Reported duration is less than one week. The contributor is 30–39, male. Texture is reported as fluid-filled. Self-categorized by the patient as a rash. Fitzpatrick phototype II; lay reviewers estimated 2 on the Monk skin tone scale. This image was taken at a distance. The patient indicates itching, bothersome appearance, pain and burning. Located on the back of the torso, arm and front of the torso: 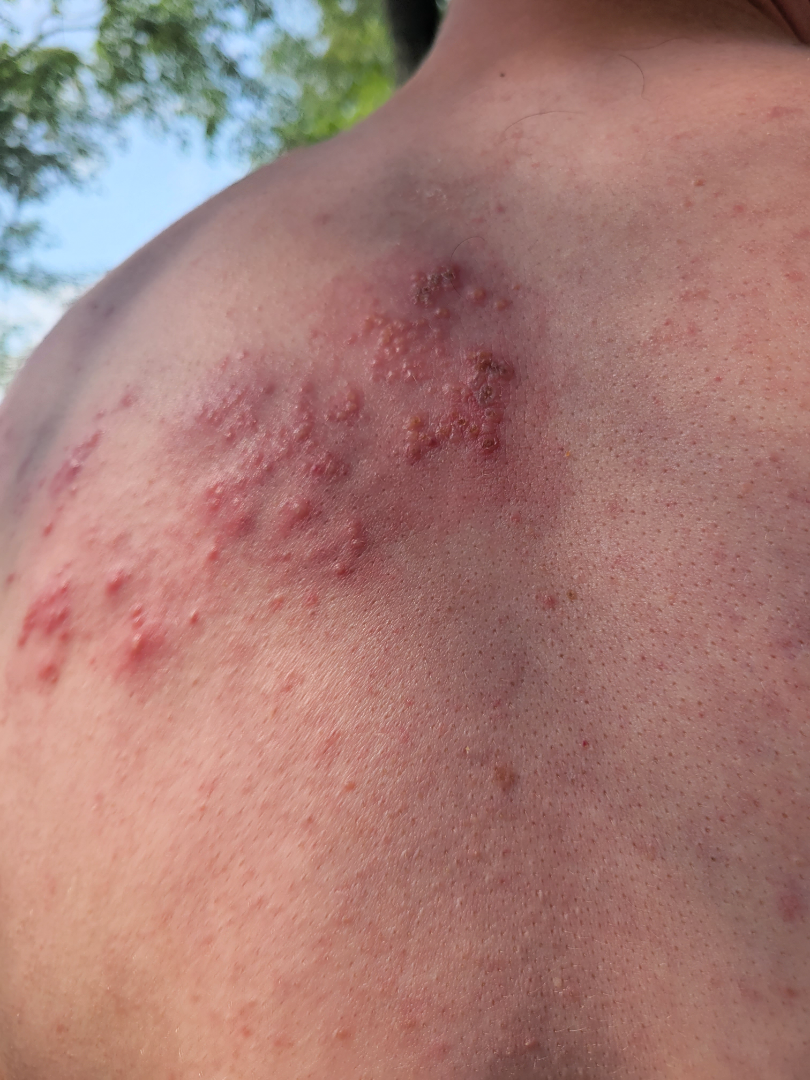Herpes Zoster and Herpes Simplex were considered with similar weight.